A close-up photograph.
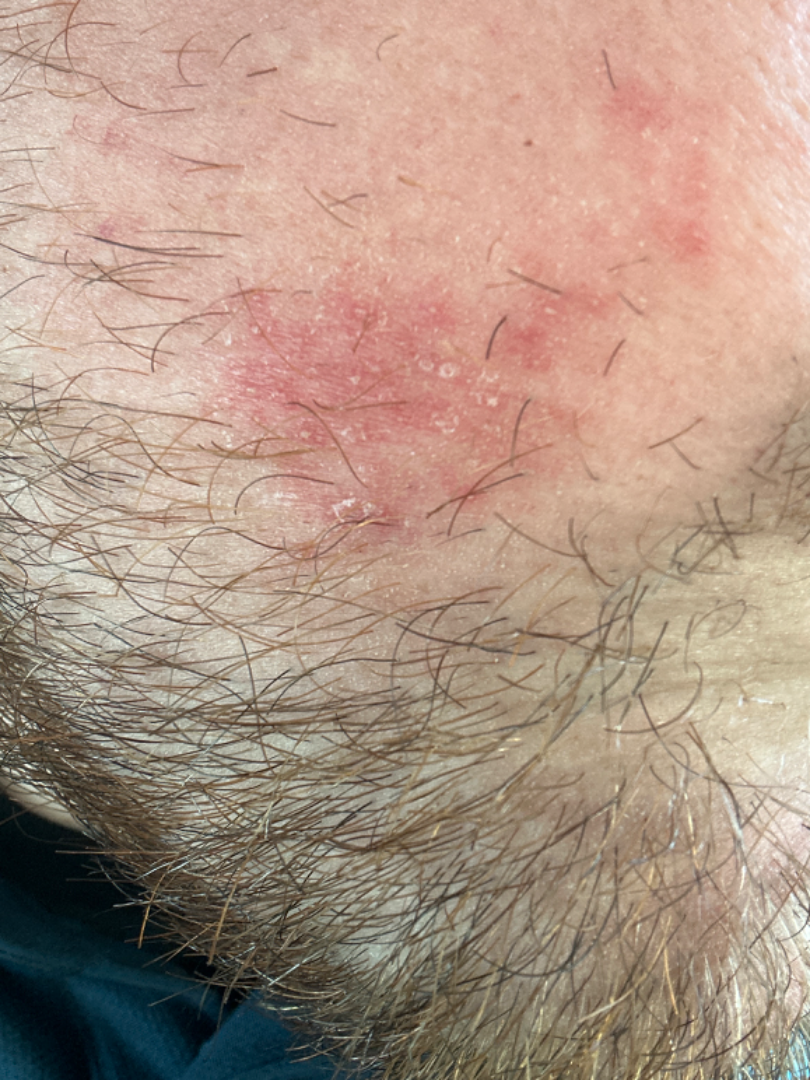Assessment:
The skin findings could not be characterized from the image.
Clinical context:
Texture is reported as raised or bumpy and rough or flaky.